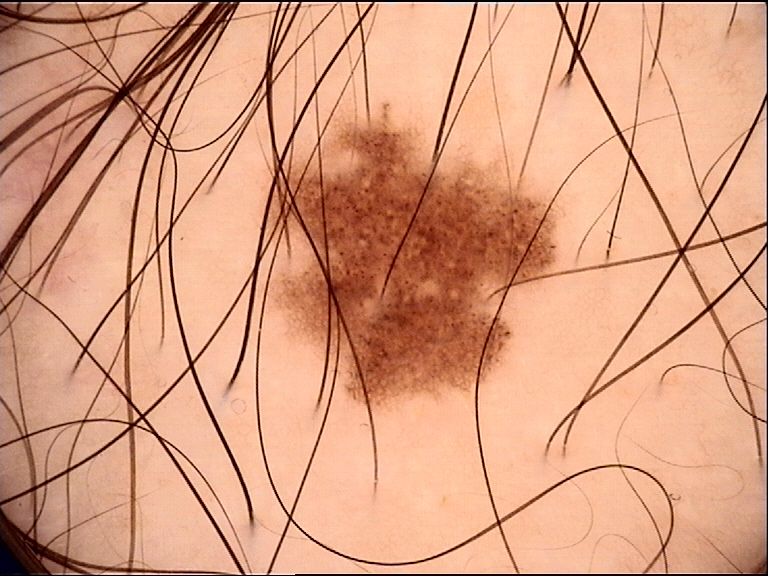| field | value |
|---|---|
| modality | dermoscopy |
| label | dysplastic junctional nevus (expert consensus) |